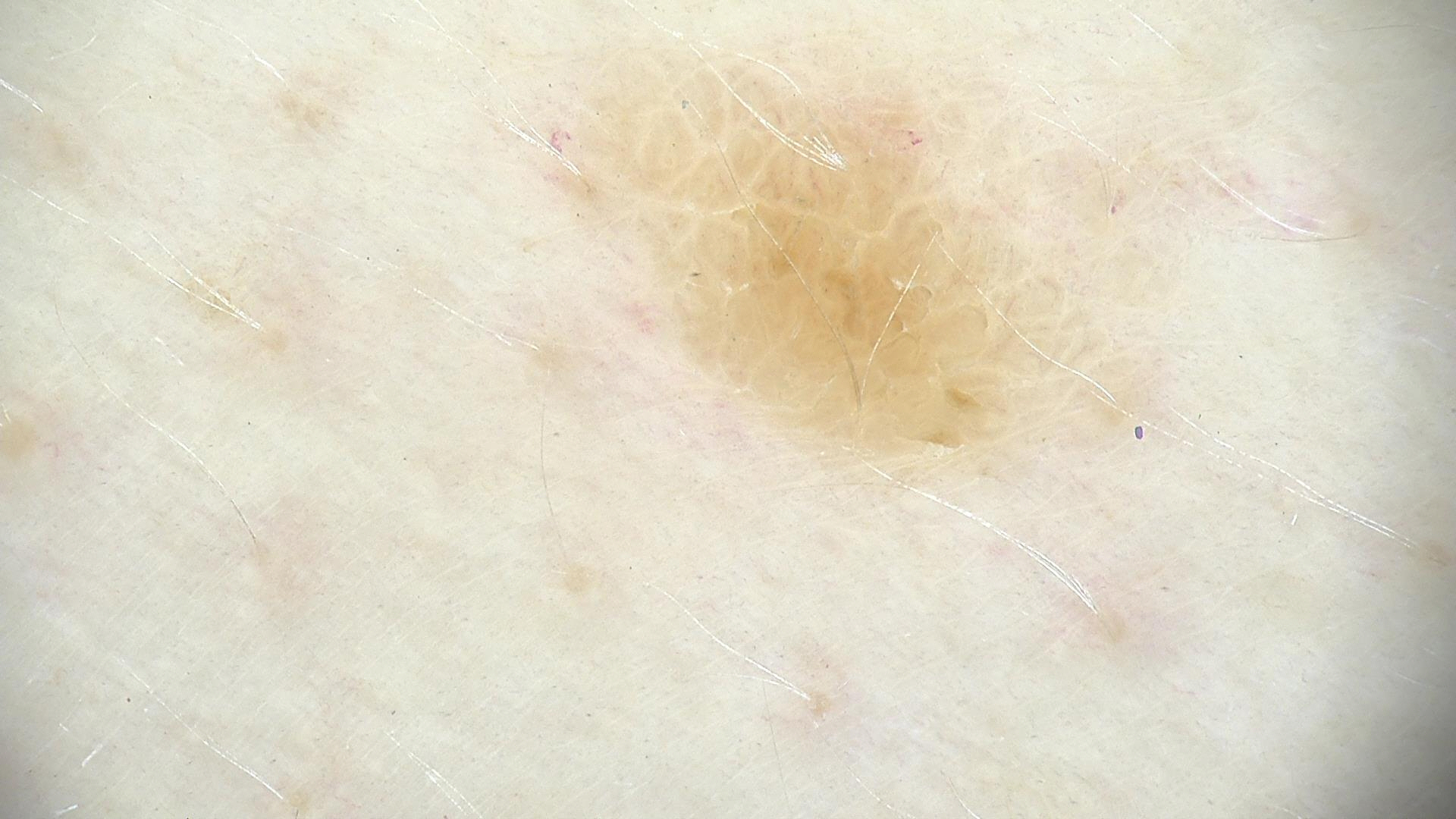The diagnosis was a seborrheic keratosis.